The leg is involved. Female contributor, age 18–29. Close-up view — 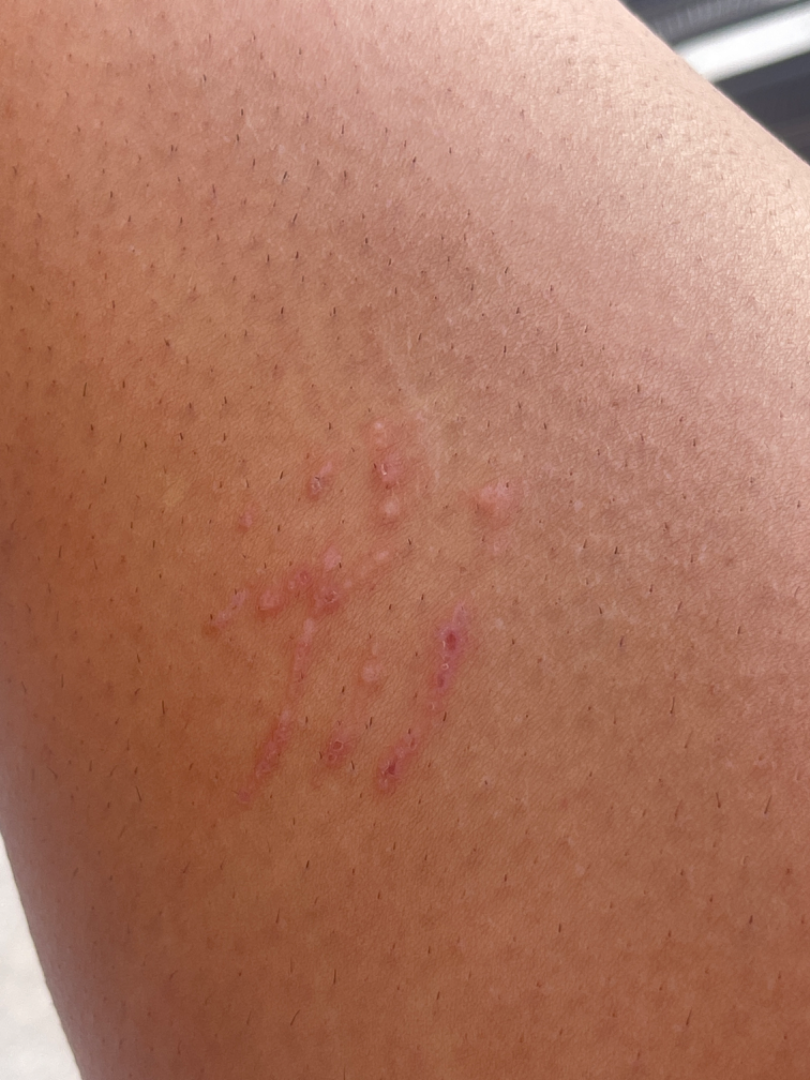surface texture = fluid-filled and raised or bumpy
reported symptoms = enlargement, burning, bothersome appearance and itching
onset = one to four weeks
associated systemic symptoms = none reported
skin tone = Fitzpatrick skin type III
clinical impression = most consistent with Animal bite - wound; also consider Abrasion, scrape, or scab; an alternative is Inflicted skin lesions